The condition has been present for about one day · the lesion involves the back of the hand · this image was taken at a distance · reported lesion symptoms include itching, burning and pain · the lesion is described as raised or bumpy and fluid-filled · the subject is 30–39, female · skin tone: Fitzpatrick I; lay graders estimated Monk skin tone scale 1 or 2 (two reviewer pools): 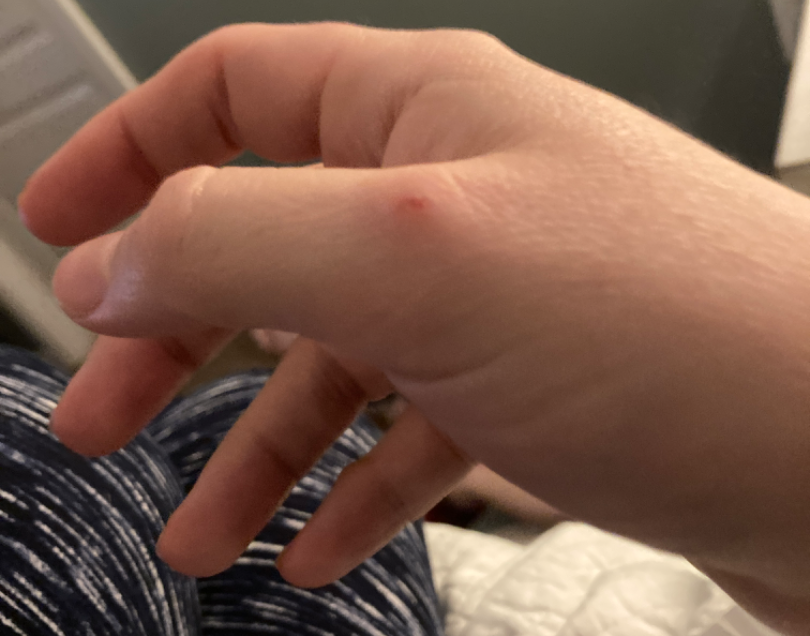Case summary:
- clinical impression · three independent reviewers: favoring Pyogenic granuloma; the differential also includes Abrasion, scrape, or scab; an alternative is Insect Bite; less probable is Hemangioma; a more distant consideration is digital myxoid cyst